This is a close-up image; the lesion involves the arm and leg; the contributor is 60–69, female: 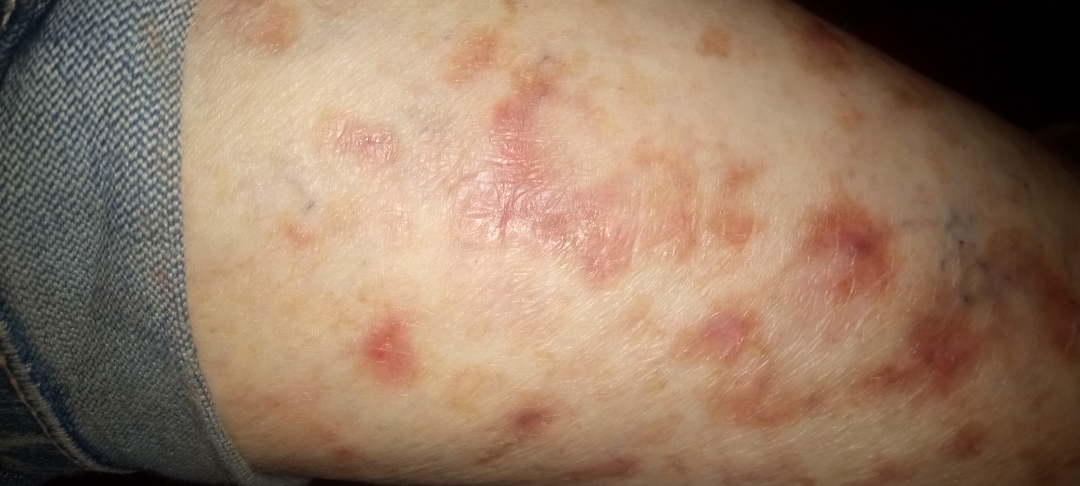Texture is reported as rough or flaky and raised or bumpy.
Symptoms reported: itching, darkening, burning, enlargement, bleeding and bothersome appearance.
Fitzpatrick skin type III; lay reviewers estimated 3 on the MST.
The patient indicates the condition has been present for more than five years.
Associated systemic symptoms include fatigue and joint pain.
The impression was split between Pigmented purpuric eruption and Stasis Dermatitis.